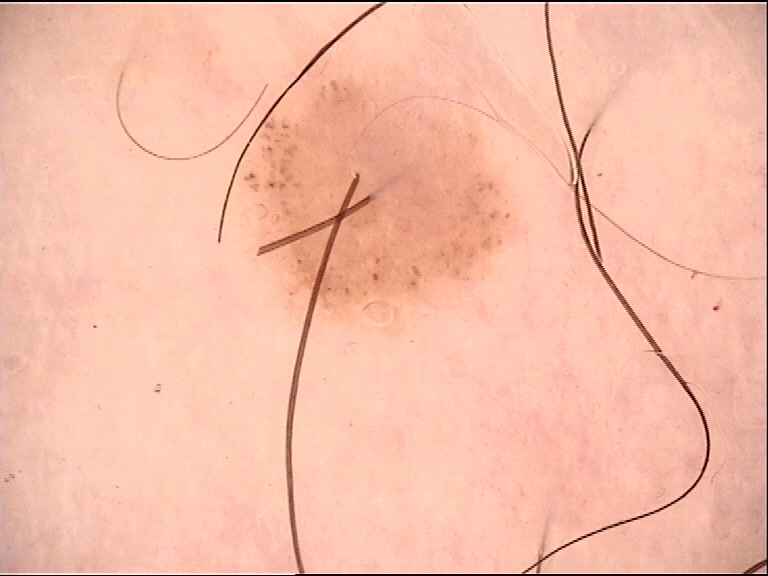image type — dermatoscopy | assessment — dysplastic junctional nevus (expert consensus).